The lesion involves the arm. This is a close-up image — 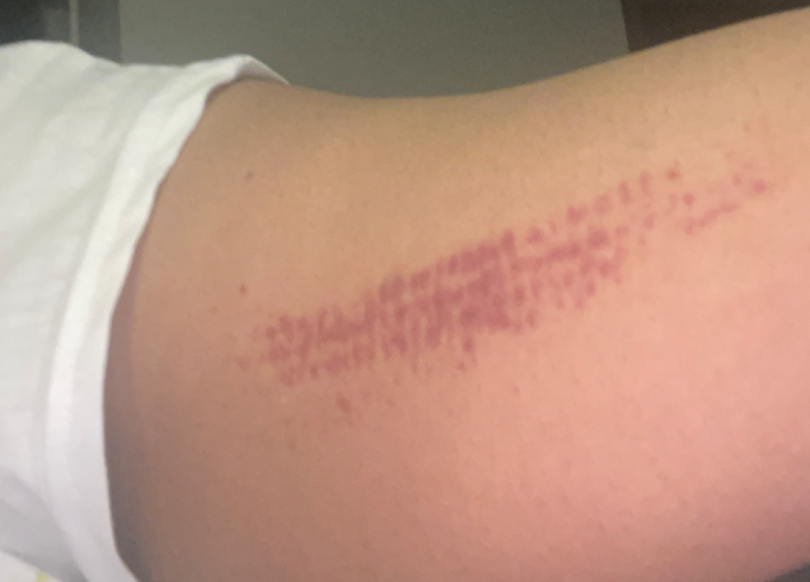Consistent with ecchymoses.